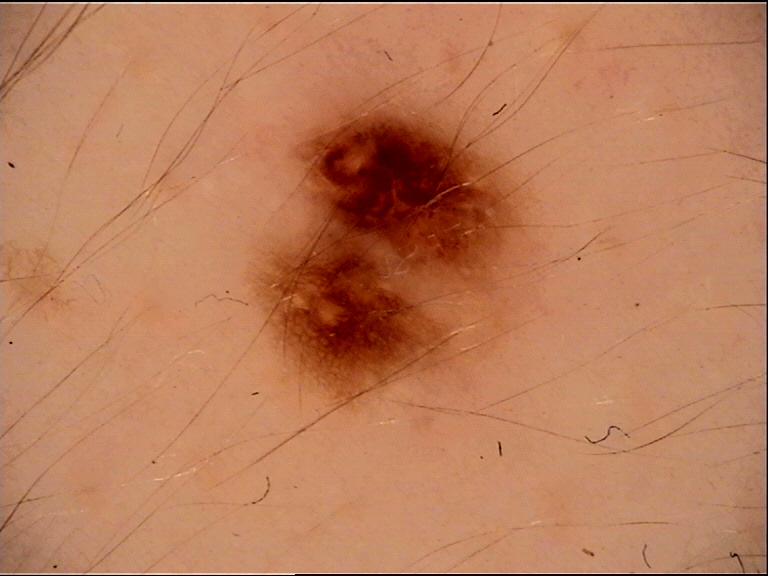Case:
– diagnosis · dysplastic junctional nevus (expert consensus)